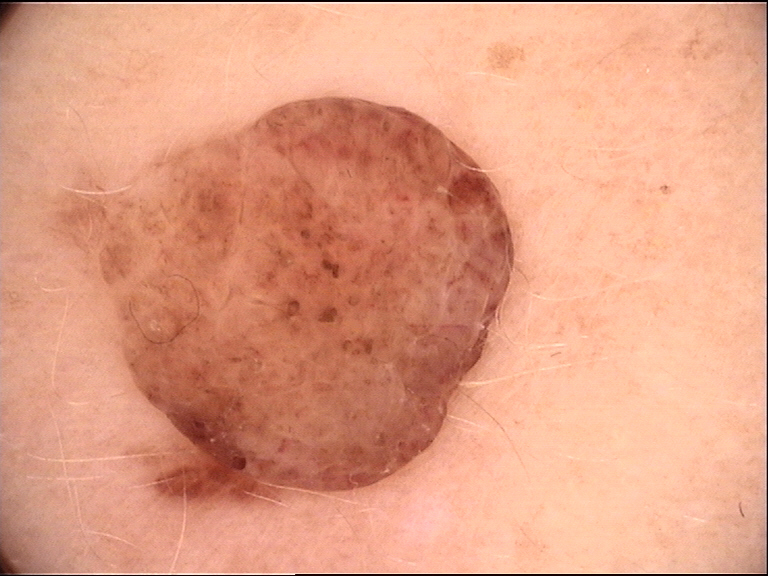Dermoscopy of a skin lesion. Consistent with a dermal nevus.